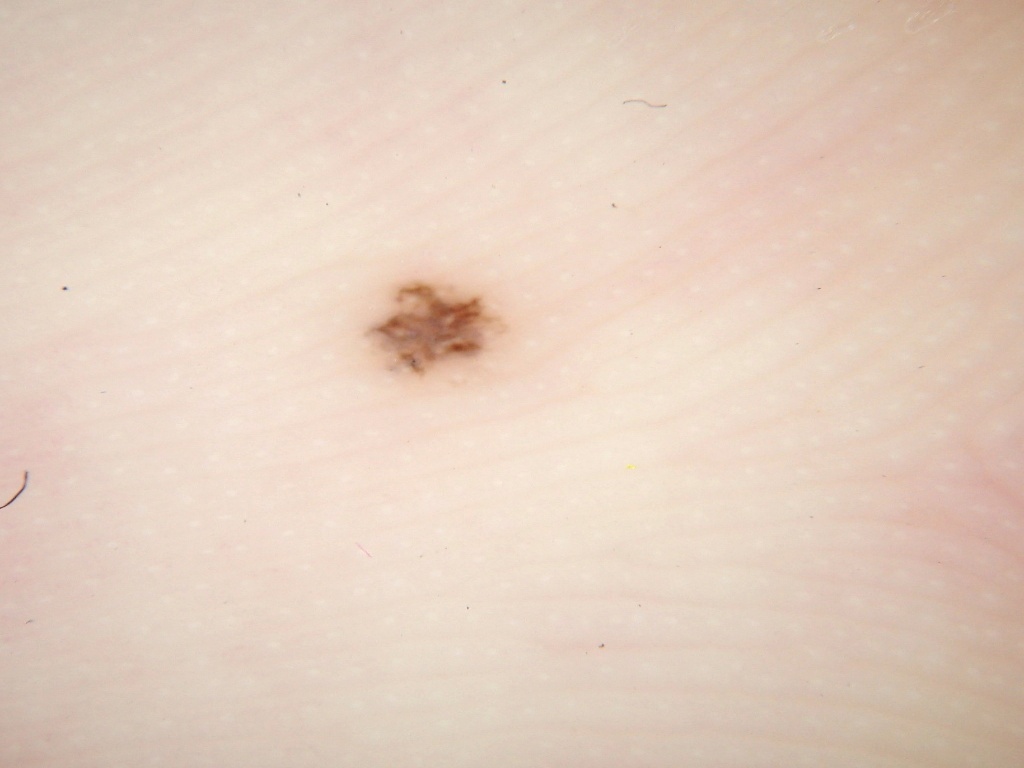A male subject, aged around 30.
A skin lesion imaged with a dermatoscope.
Dermoscopic examination shows no globules, negative network, milia-like cysts, streaks, or pigment network.
With coordinates (x1, y1, x2, y2), the lesion's extent is 366/280/505/376.
A small lesion occupying a minor part of the field.
Consistent with a melanocytic nevus, a benign skin lesion.